By self-report, a personal history of cancer, a personal history of skin cancer, and no sunbed use · few moles overall by the patient's own estimate · referred for assessment of suspected basal cell carcinoma · the patient says their skin tans without first burning · a female subject aged 60 · a skin lesion imaged with a dermatoscope: 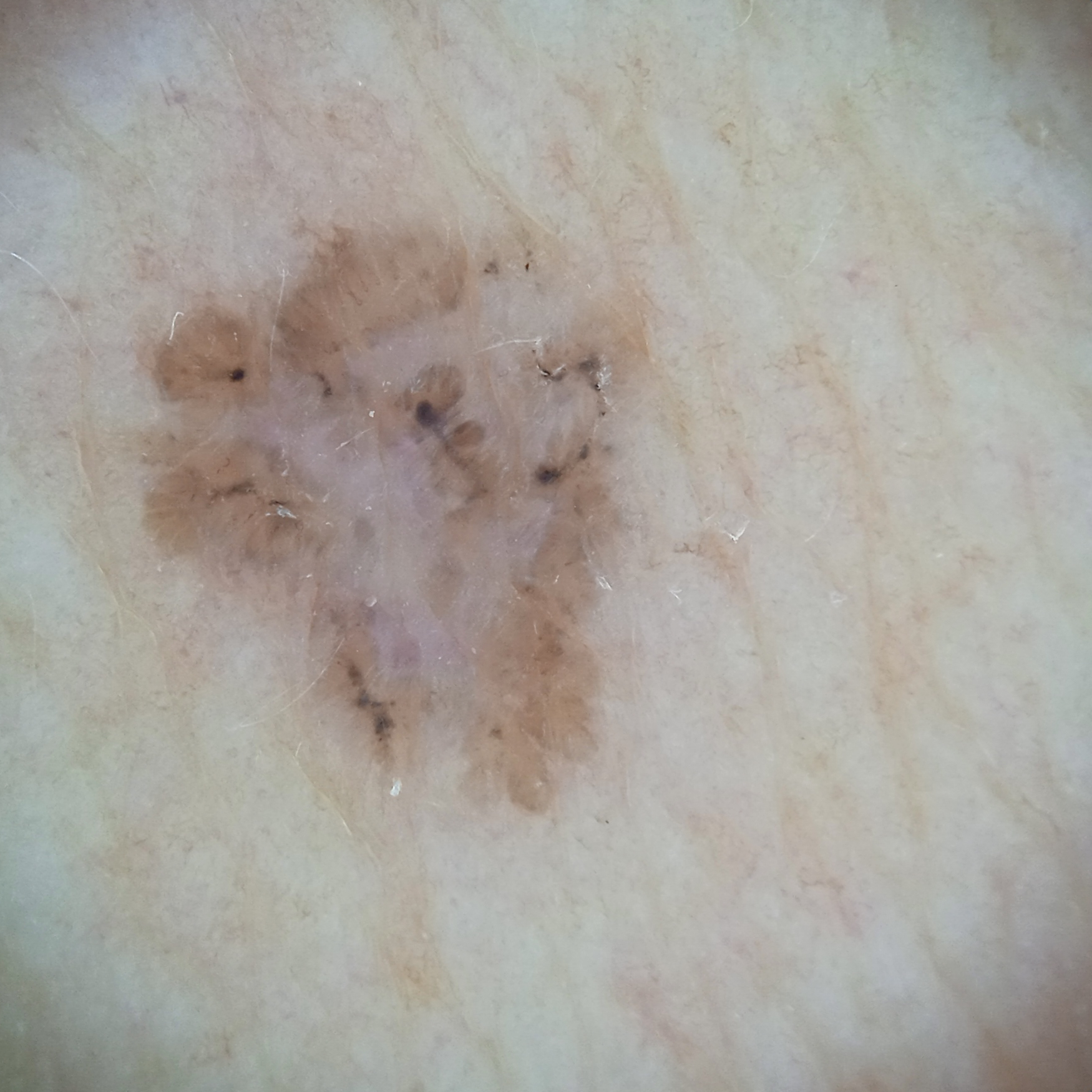Summary:
The lesion is on the torso. Measuring roughly 7.2 mm.
Conclusion:
The consensus diagnosis for this lesion was a basal cell carcinoma.